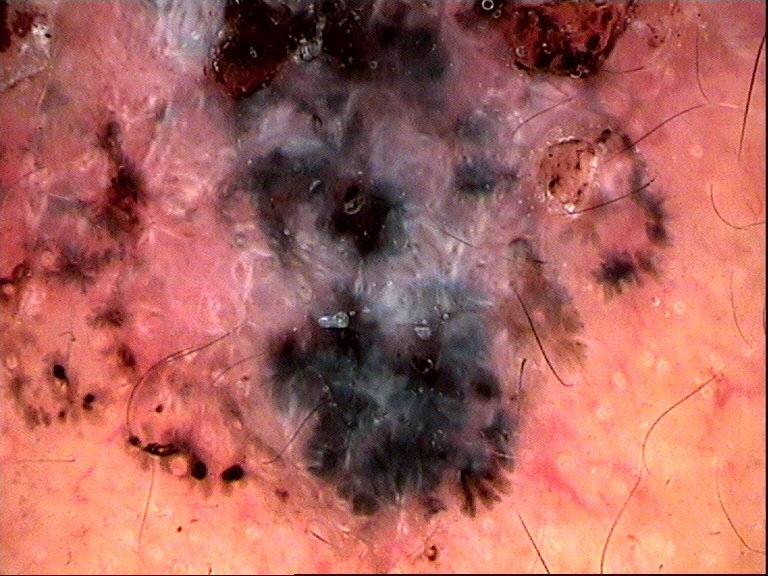diagnostic label: basal cell carcinoma (biopsy-proven).